The affected area is the head or neck · the photograph is a close-up of the affected area · female subject, age 50–59: 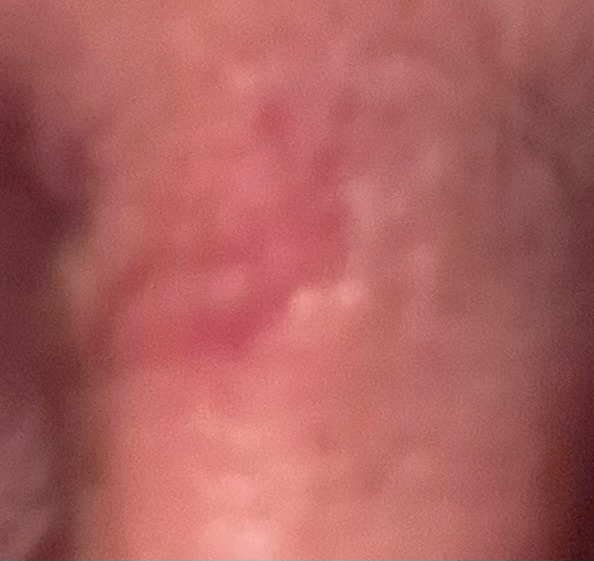No differential diagnosis could be assigned on photographic review. Reported duration is three to twelve months. The patient notes bothersome appearance and itching. No associated systemic symptoms reported. The patient notes the lesion is rough or flaky and raised or bumpy. Skin tone: self-reported FST I; non-clinician graders estimated Monk skin tone scale 3.